The subject is a male aged 8-12; a skin lesion imaged with a dermatoscope: 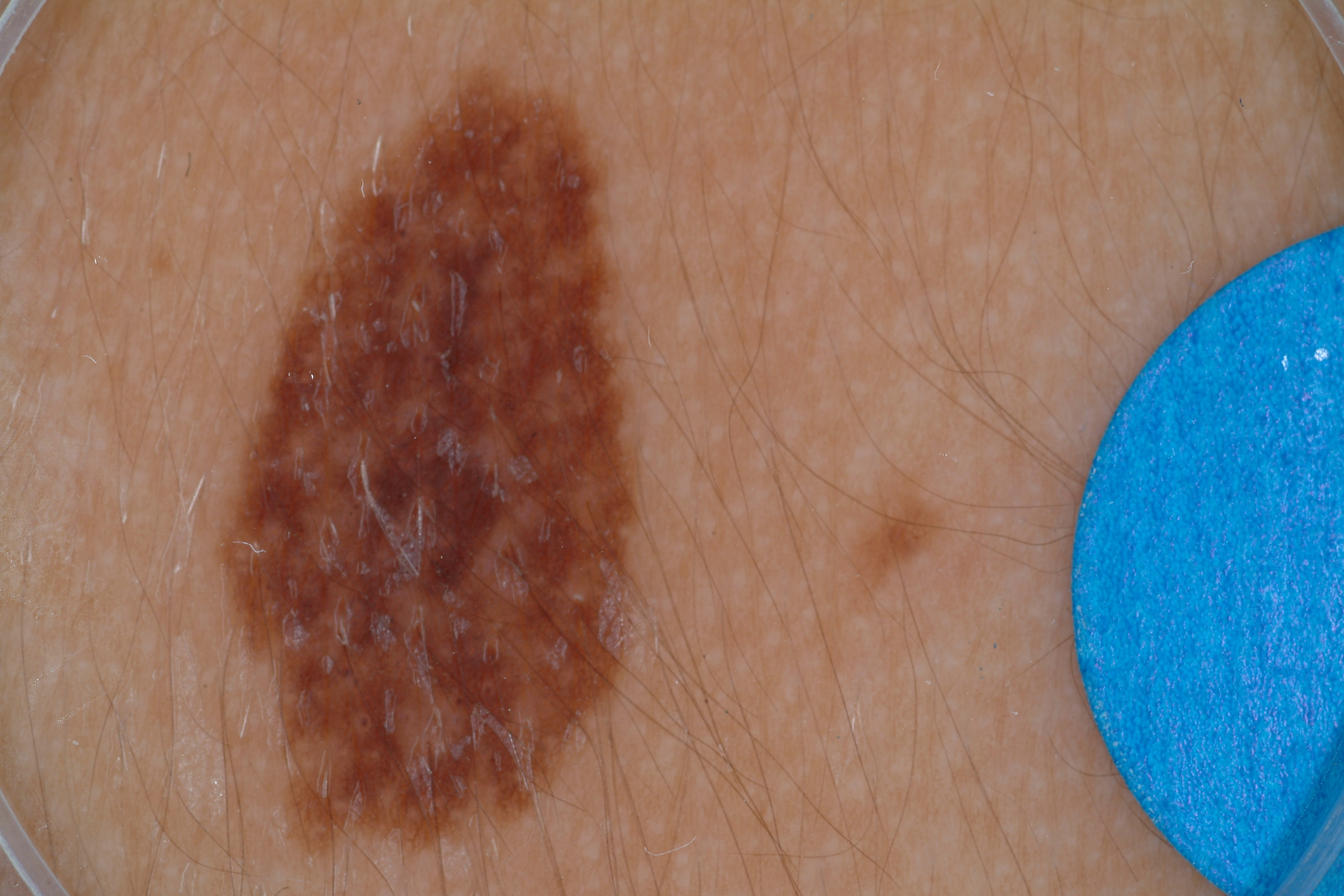{"lesion_extent": {"approx_field_fraction_pct": 20}, "lesion_location": {"bbox_xyxy": [215, 65, 643, 857]}, "dermoscopic_features": {"present": ["pigment network"], "absent": ["milia-like cysts", "streaks", "globules", "negative network"]}, "diagnosis": {"name": "melanocytic nevus", "malignancy": "benign", "lineage": "melanocytic", "provenance": "clinical"}}